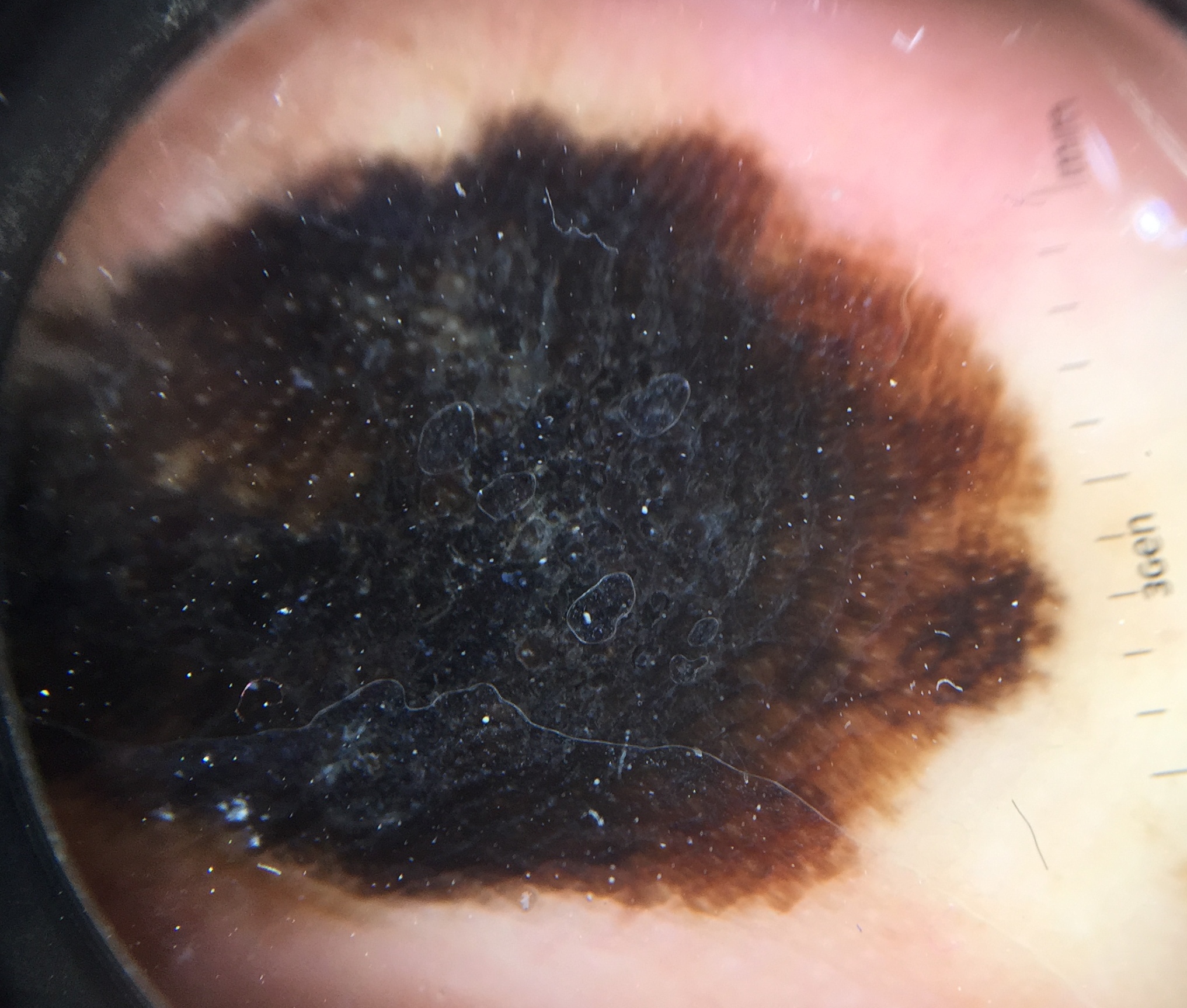The biopsy diagnosis was an acral lentiginous melanoma.